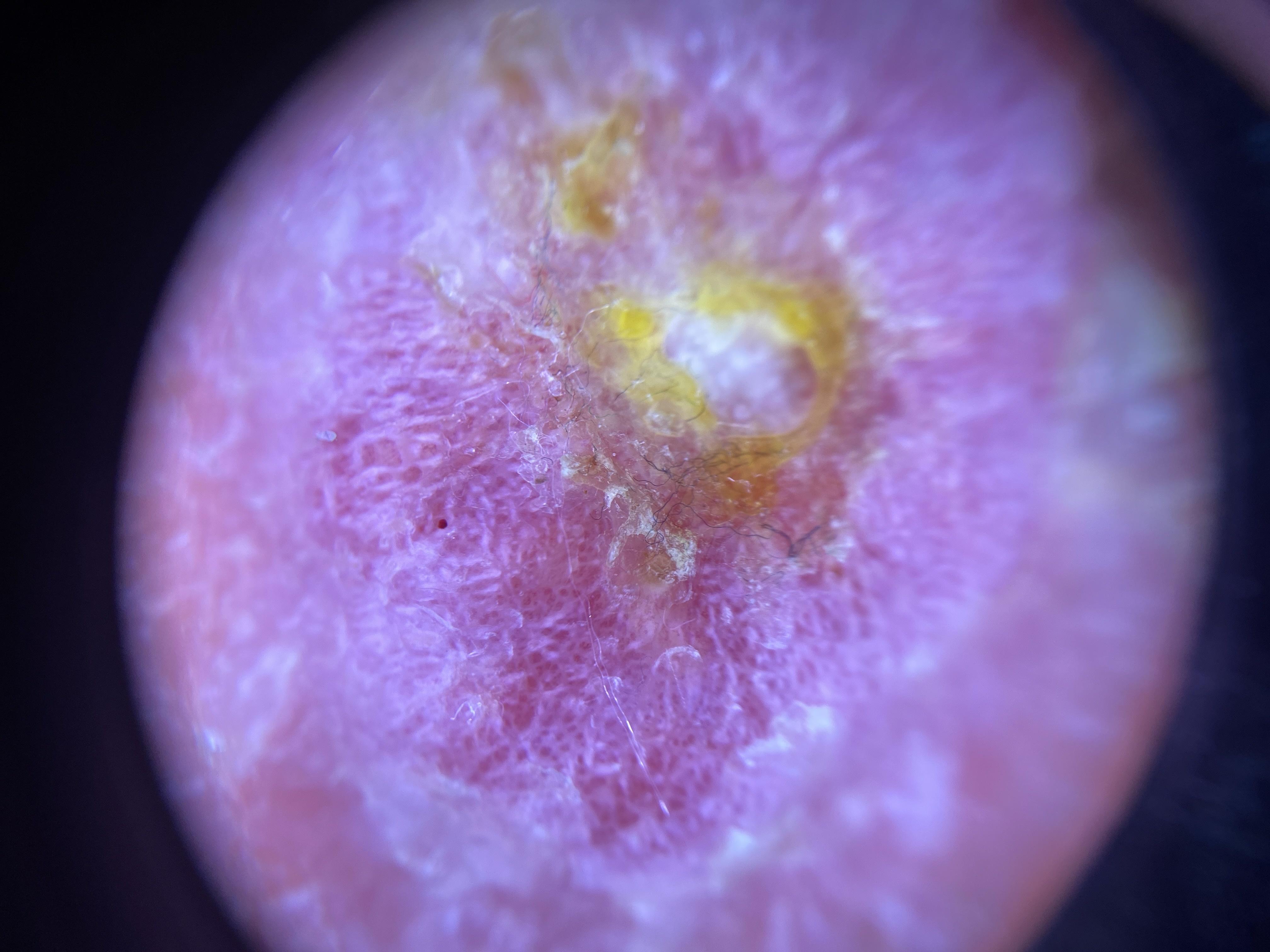Contact-polarized dermoscopy of a skin lesion. The patient was assessed as skin type II. The lesion was found on a lower extremity. Histopathology confirmed a squamous cell carcinoma.